A close-up photograph · the patient considered this a rash · the lesion is described as raised or bumpy · skin tone: FST II; human graders estimated Monk Skin Tone 3–4 · the lesion is associated with itching · the lesion involves the arm: 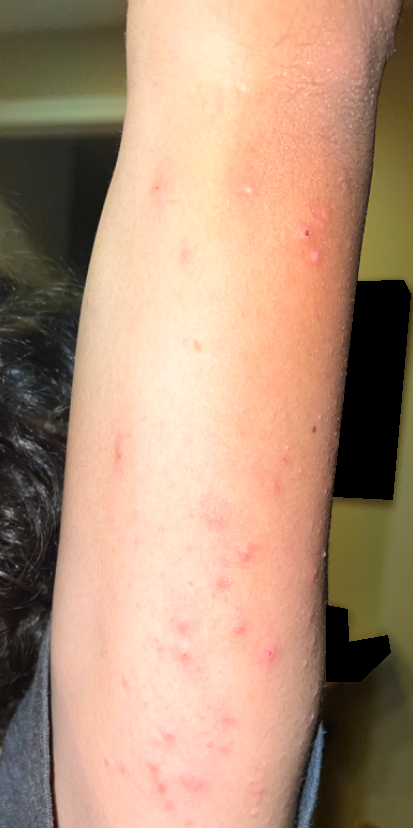Impression: The reviewing dermatologist's impression was: most consistent with Folliculitis.